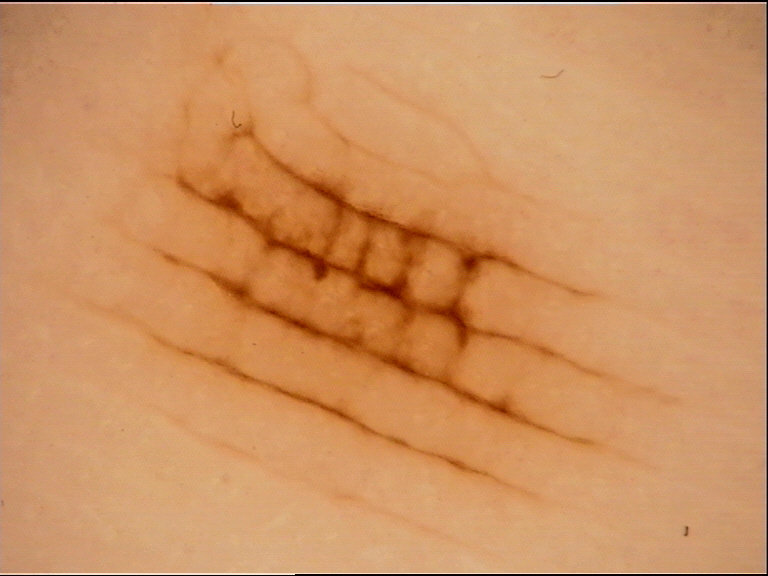Findings:
• modality — dermatoscopy
• subtype — banal
• class — acral junctional nevus (expert consensus)